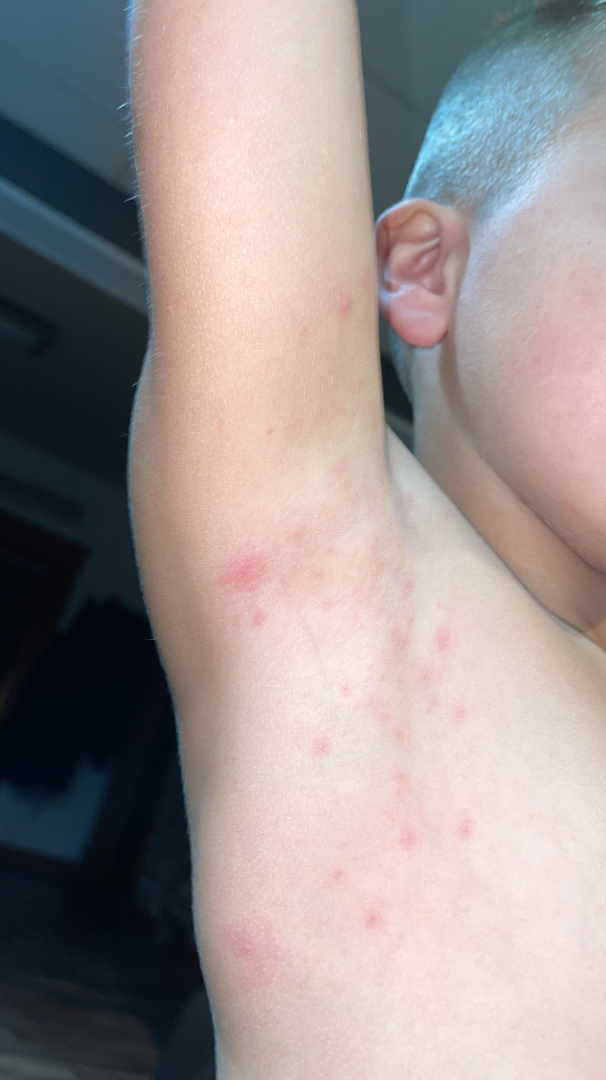Texture is reported as raised or bumpy. The contributor notes itching and pain. Reported duration is one to three months. The lesion involves the arm and back of the torso. A close-up photograph. The patient described the issue as a rash. The reviewing clinician's impression was: Molluscum Contagiosum (favored); Folliculitis (considered); Papular acrodermatitis of childhood (considered).